A dermoscopic view of a skin lesion:
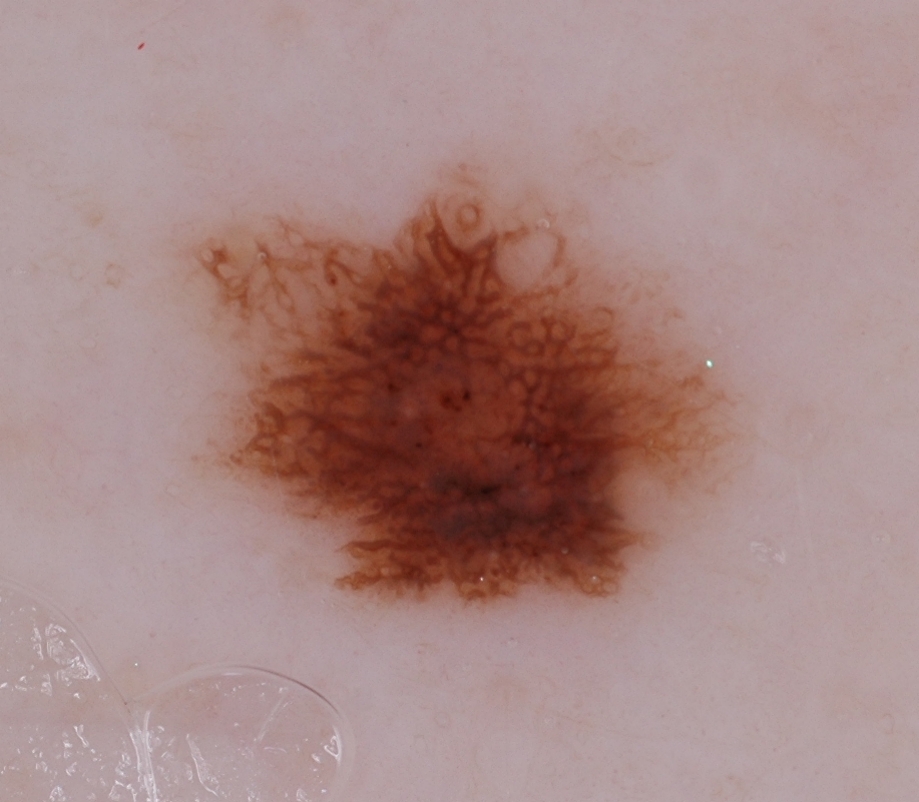Case summary:
– location — [180, 160, 731, 613]
– diagnostic label — a melanocytic nevus